Dermoscopy of a skin lesion · a female subject aged 78 · acquired for a research image collection, with no referral diagnosis:
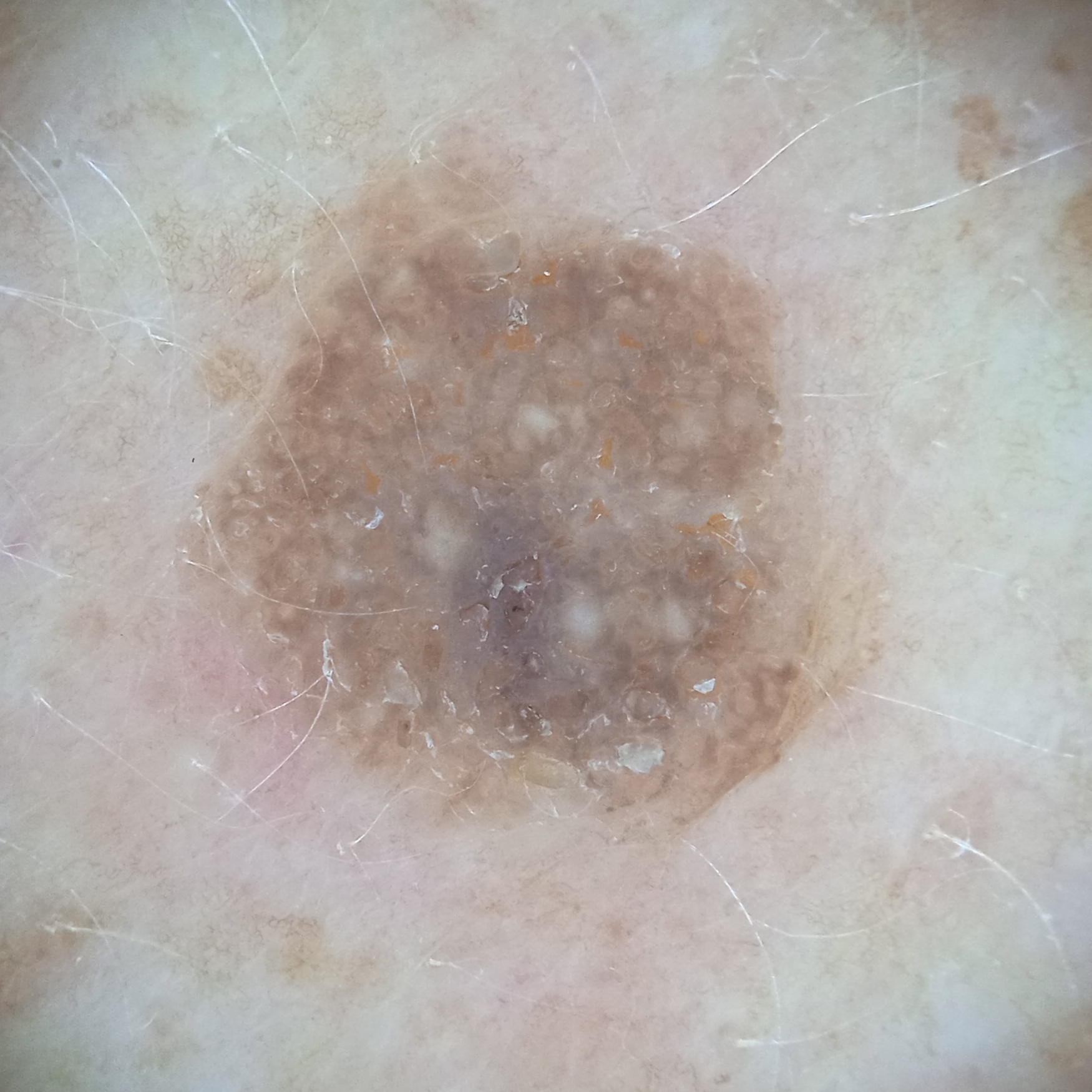The lesion is located on the back.
The lesion measures approximately 7.3 mm.
The consensus diagnosis for this lesion was a seborrheic keratosis.